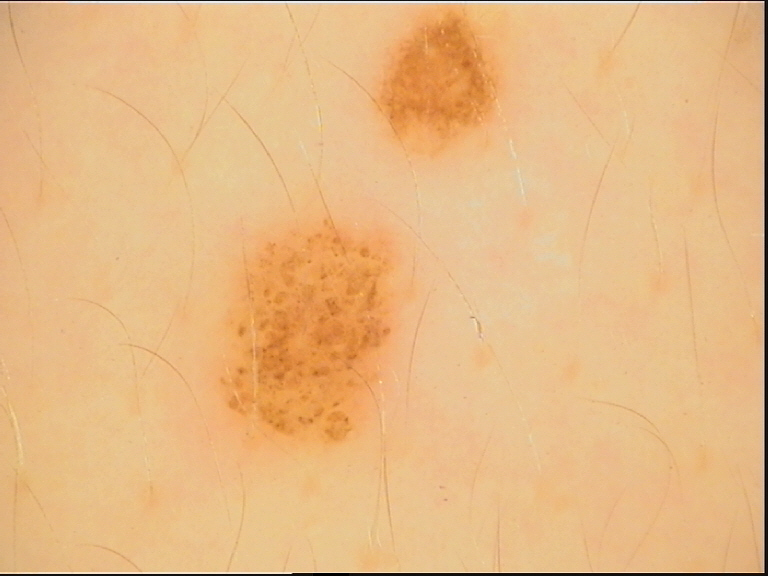Summary:
A dermoscopy image of a single skin lesion.
Impression:
Labeled as a benign lesion — a dysplastic compound nevus.